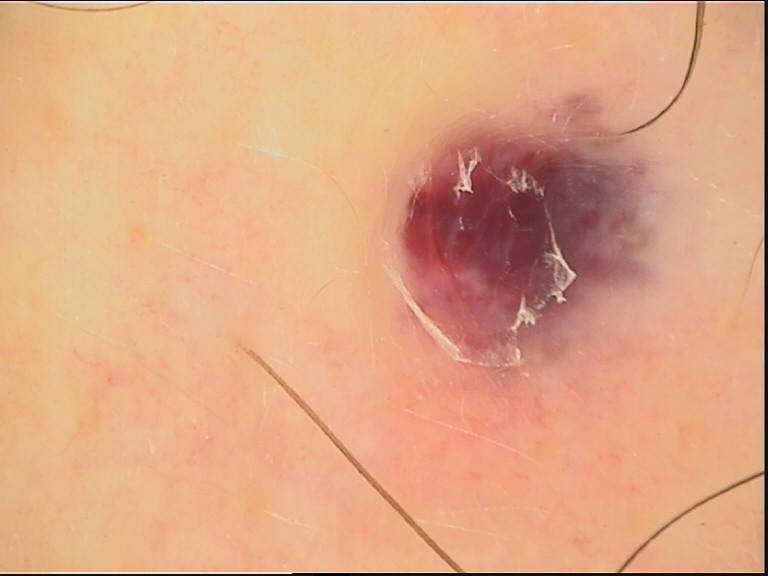The morphology is that of a vascular lesion. Consistent with a hemangioma.